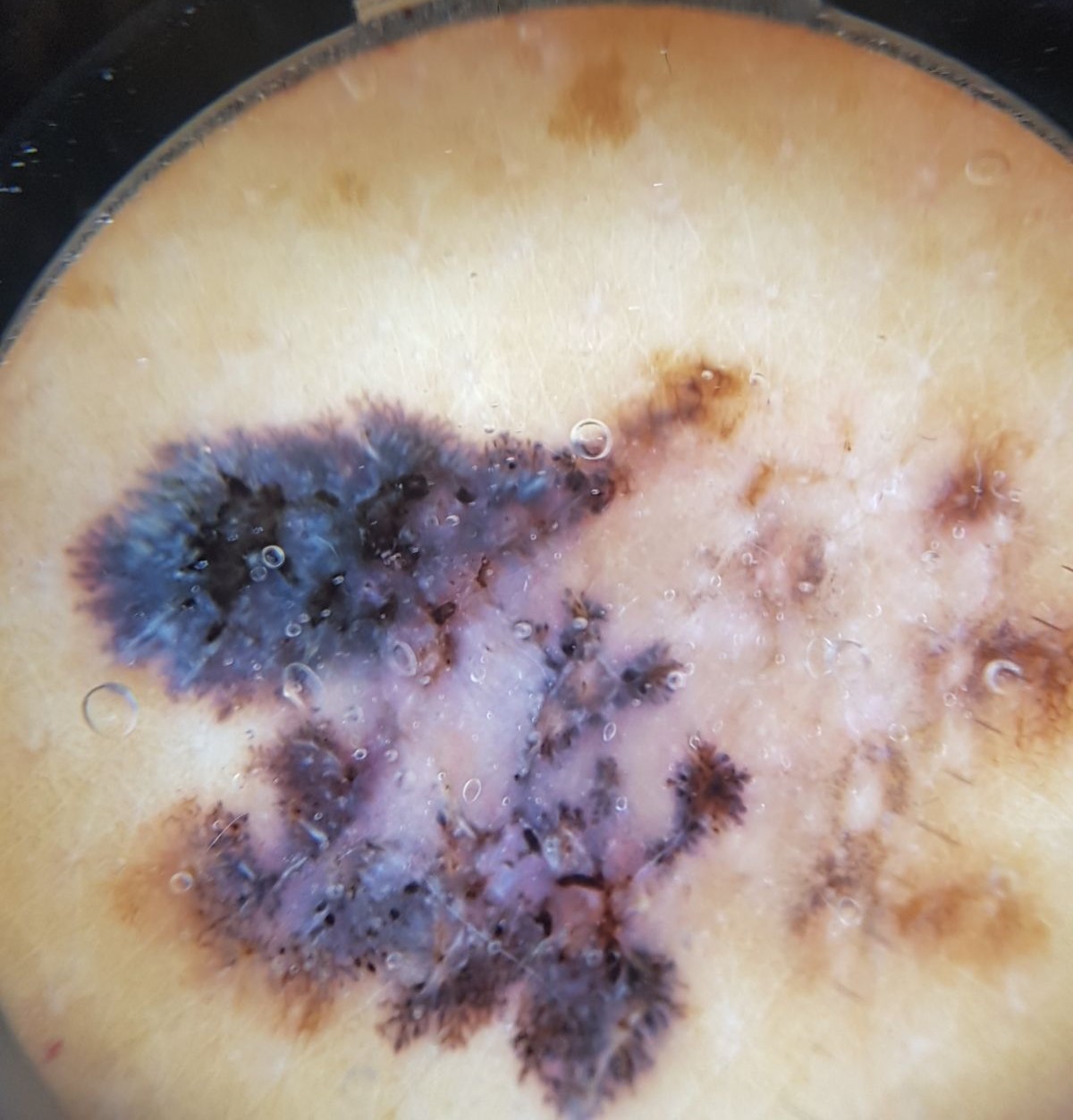diagnostic label: melanoma (biopsy-proven).